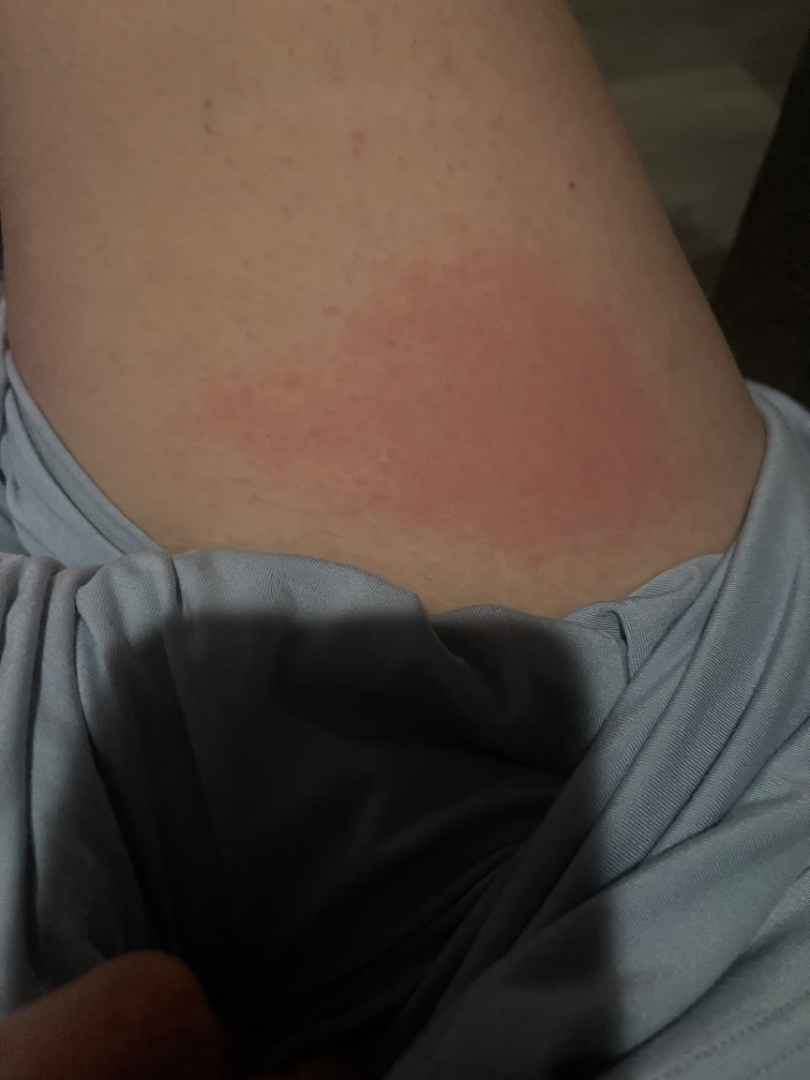<case>
<body_site>front of the torso, leg</body_site>
<patient>female, age 40–49</patient>
<shot_type>close-up</shot_type>
<differential>
  <leading>Contact dermatitis</leading>
  <unlikely>Acute dermatitis, NOS; Irritant Contact Dermatitis; Urticaria; Allergic Contact Dermatitis; Hypersensitivity</unlikely>
</differential>
</case>